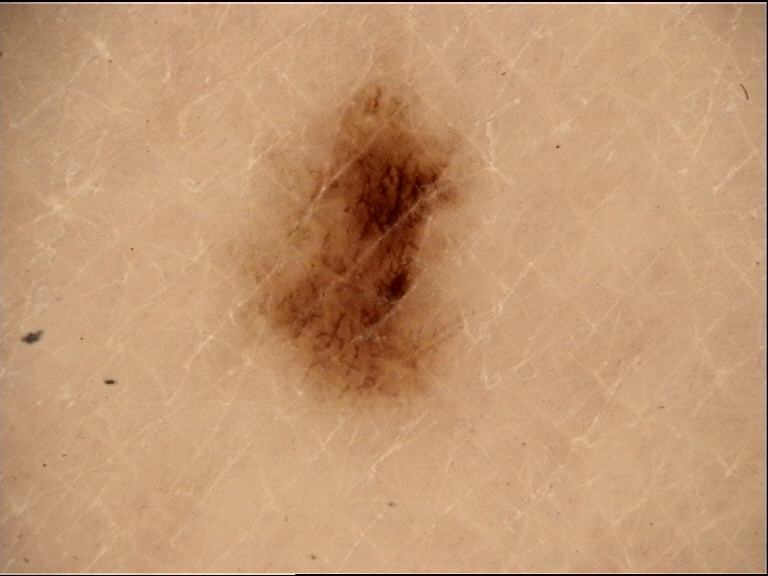Dermoscopy of a skin lesion.
Labeled as a benign lesion — a dysplastic junctional nevus.